Few moles overall by the patient's own estimate; on a questionnaire the patient reported a personal history of cancer, no prior organ transplant, and no personal history of skin cancer; a clinical photograph of a skin lesion; a female subject 84 years old; the patient says their skin tans without first burning; referred for assessment of suspected basal cell carcinoma: 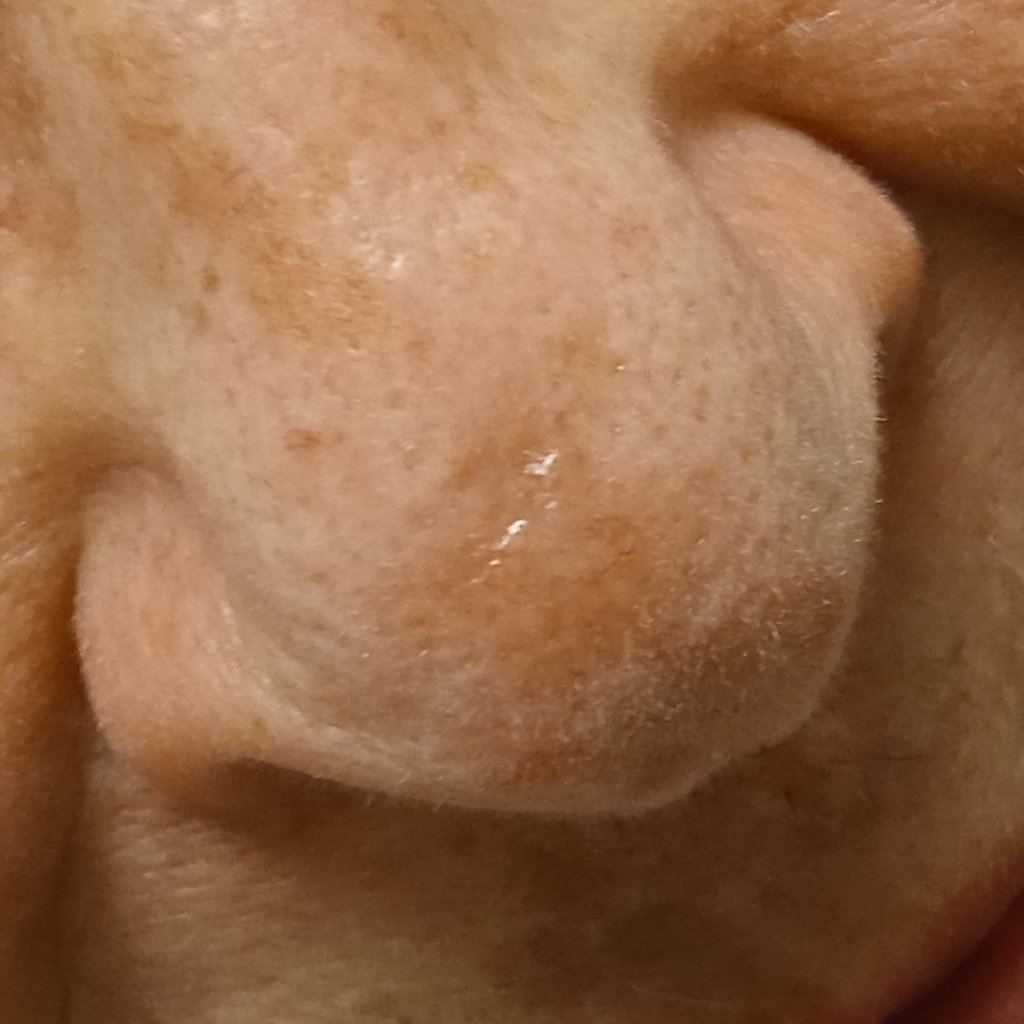Case:
– diagnosis · basal cell carcinoma (biopsy-proven)